The lesion involves the front of the torso and leg. The photograph was taken at a distance.
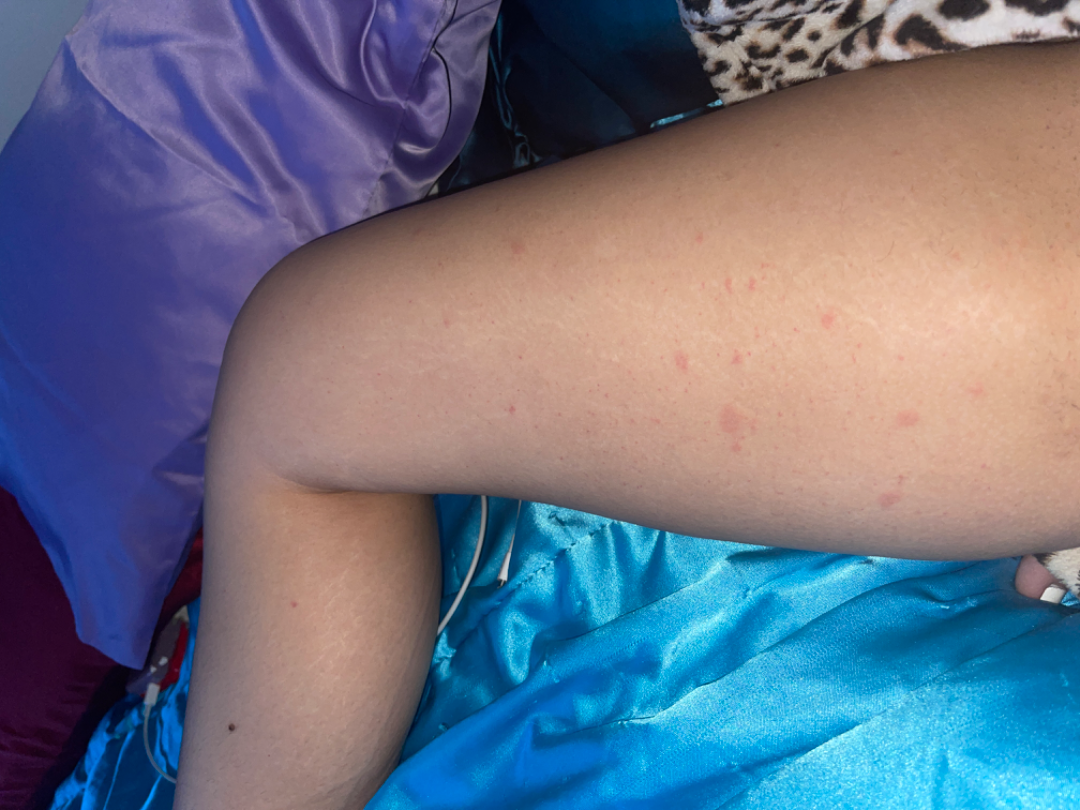Clinical context:
FST III; human graders estimated MST 2 or 4. The patient described the issue as a rash. Texture is reported as raised or bumpy.
Assessment:
On independent review by the dermatologists: Viral Exanthem (most likely); Pityriasis rosea (remote); Allergic Contact Dermatitis (remote); Drug Rash (remote); Hypersensitivity (remote).